A skin lesion imaged with a dermatoscope — 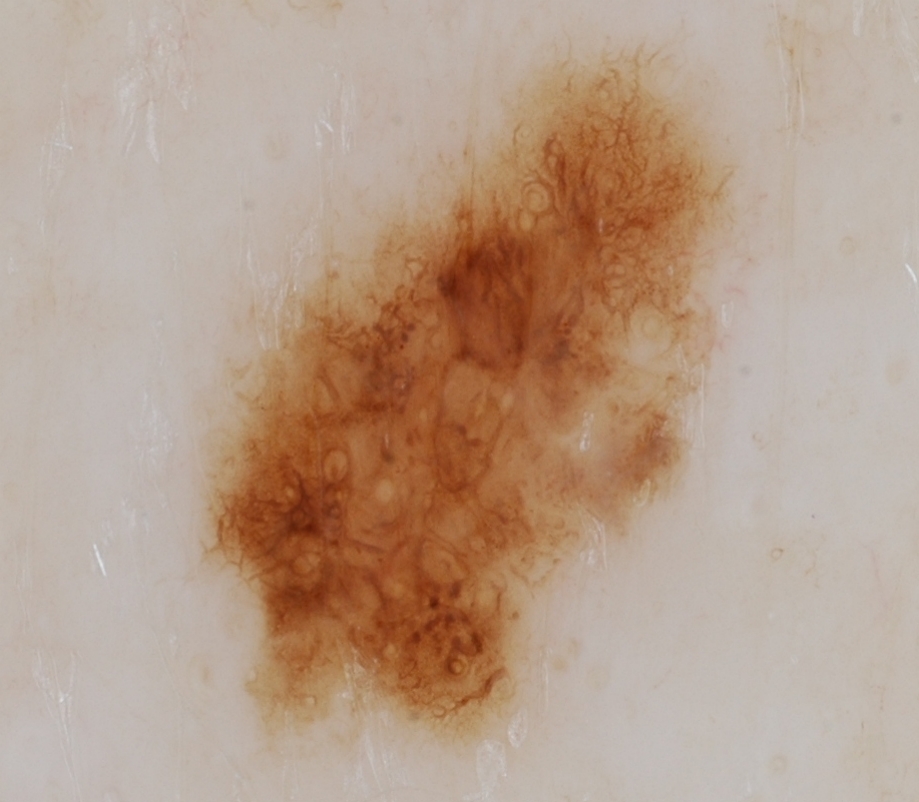The lesion's extent is 200 49 732 742.
The lesion covers approximately 31% of the dermoscopic field.
The dermoscopic pattern shows globules and pigment network.
Biopsy-confirmed as a melanoma.